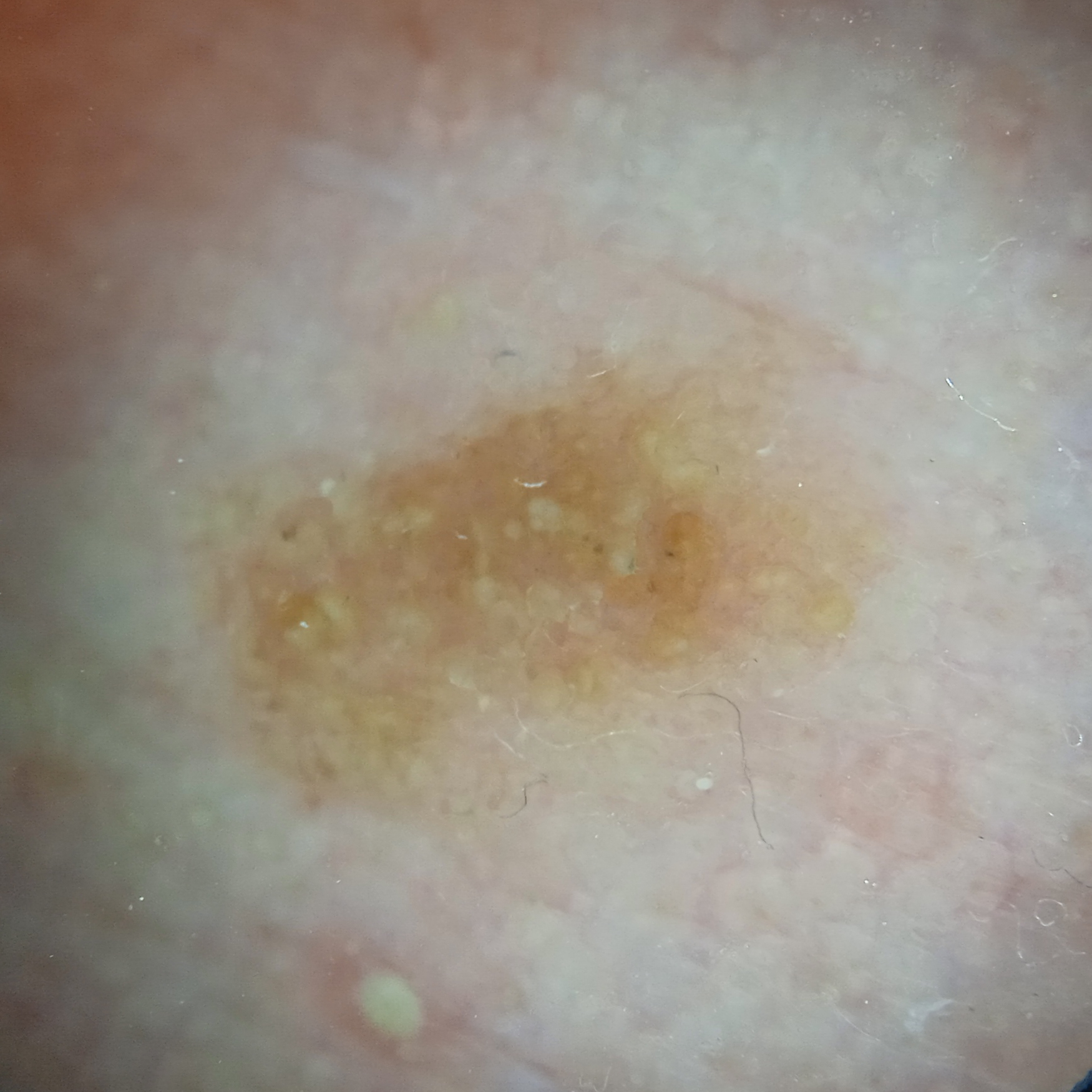A skin lesion imaged with a dermatoscope.
The patient says their skin reddens painfully with sun exposure.
Imaged for a research study, with no referral diagnosis recorded.
Located on the face.
Dermatologist review favored an actinic keratosis.